This is a close-up image:
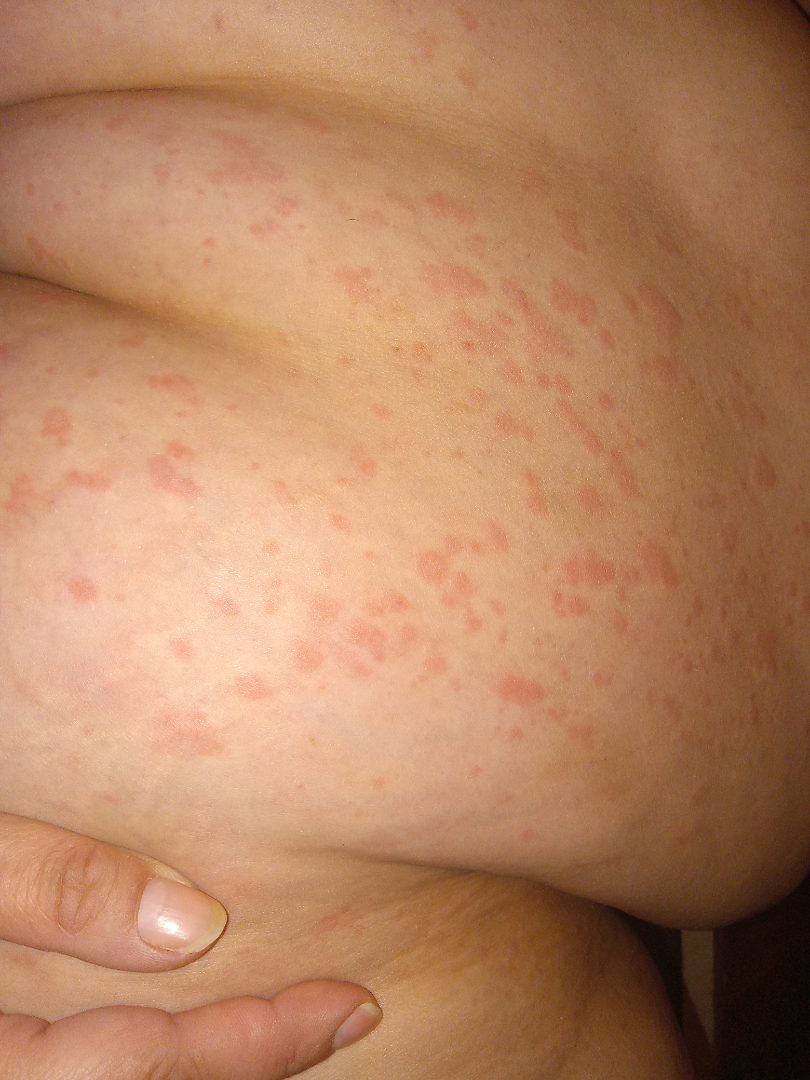assessment=the impression was split between Psoriasis, Pityriasis rosea and Drug Rash